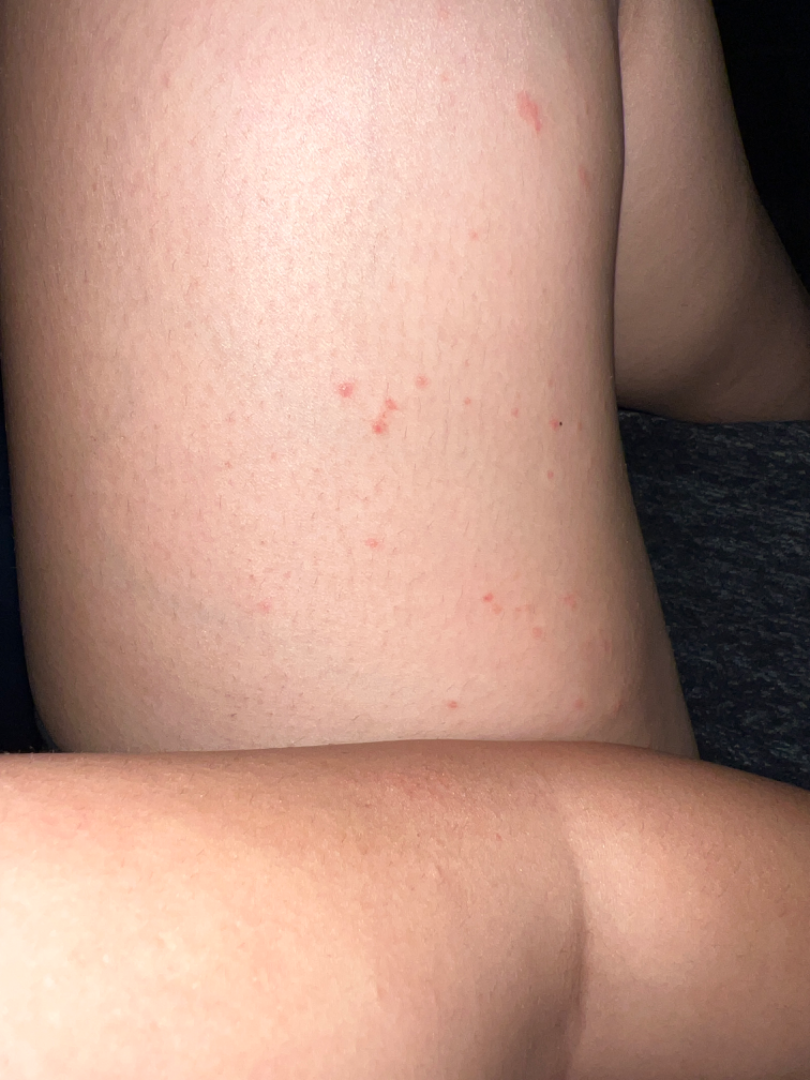Female patient, age 18–29. Reported lesion symptoms include enlargement and itching. The photograph was taken at an angle. Texture is reported as raised or bumpy. The patient reports the condition has been present for more than five years. Skin tone: Fitzpatrick II. The leg, arm, back of the hand and back of the torso are involved. The patient described the issue as a rash. On teledermatology review: favoring Folliculitis; less probable is Urticaria; a remote consideration is Insect Bite; less likely is Eczema; a more distant consideration is Allergic Contact Dermatitis.